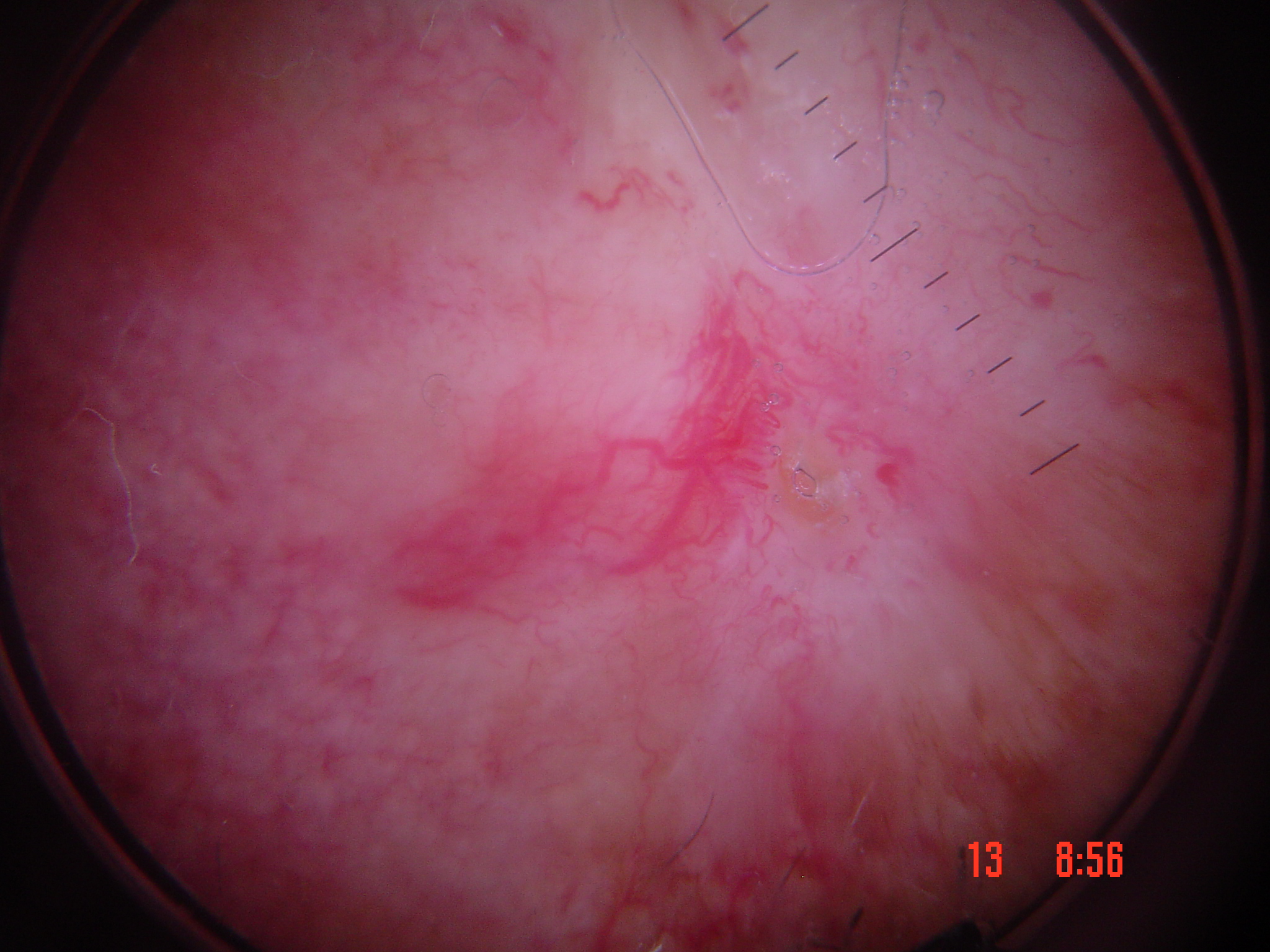pathology: basal cell carcinoma (biopsy-proven).